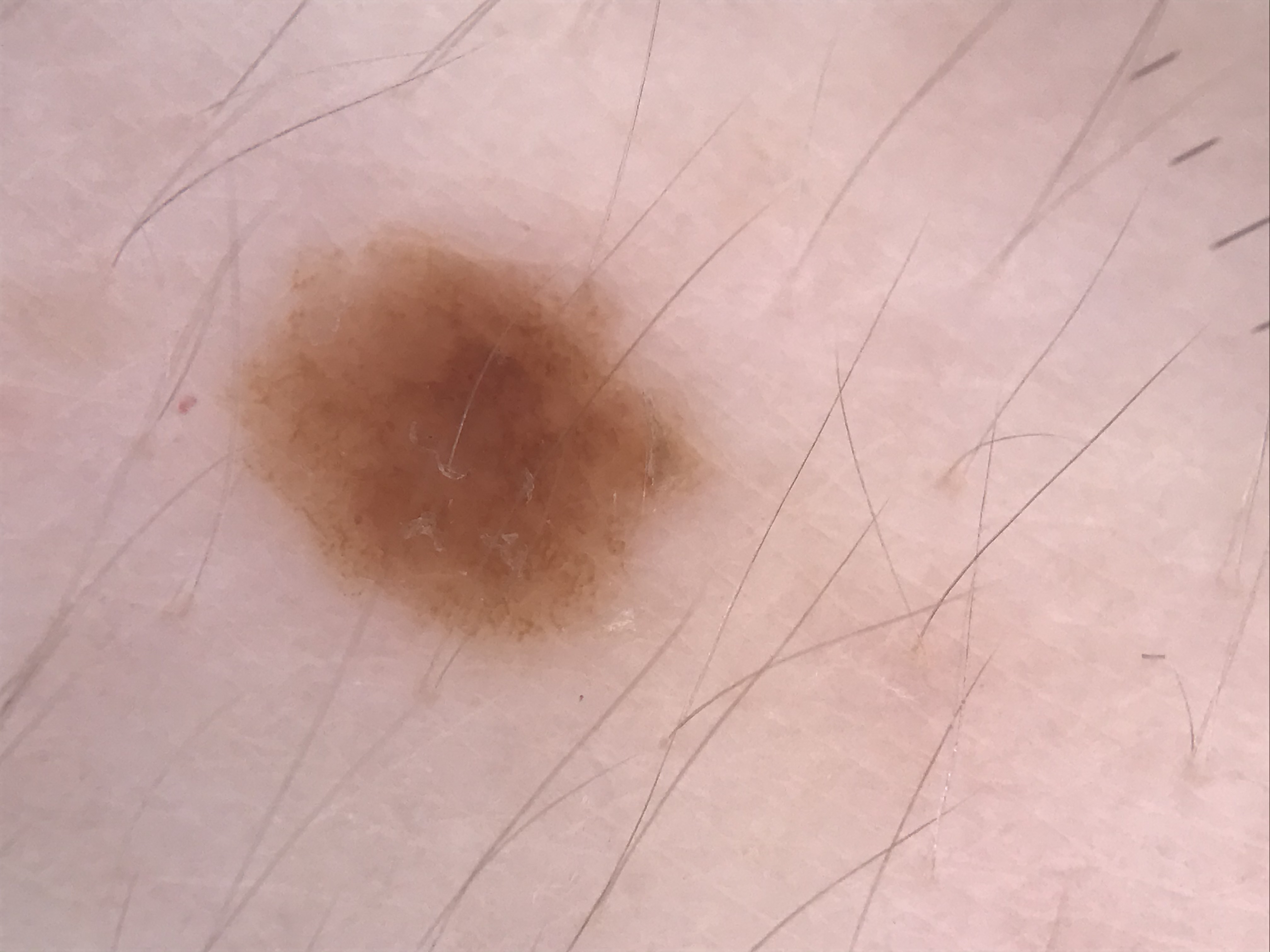A dermoscopic photograph of a skin lesion. The diagnosis was a benign lesion — a dysplastic junctional nevus.